A dermatoscopic image of a skin lesion; the subject is a female aged approximately 20:
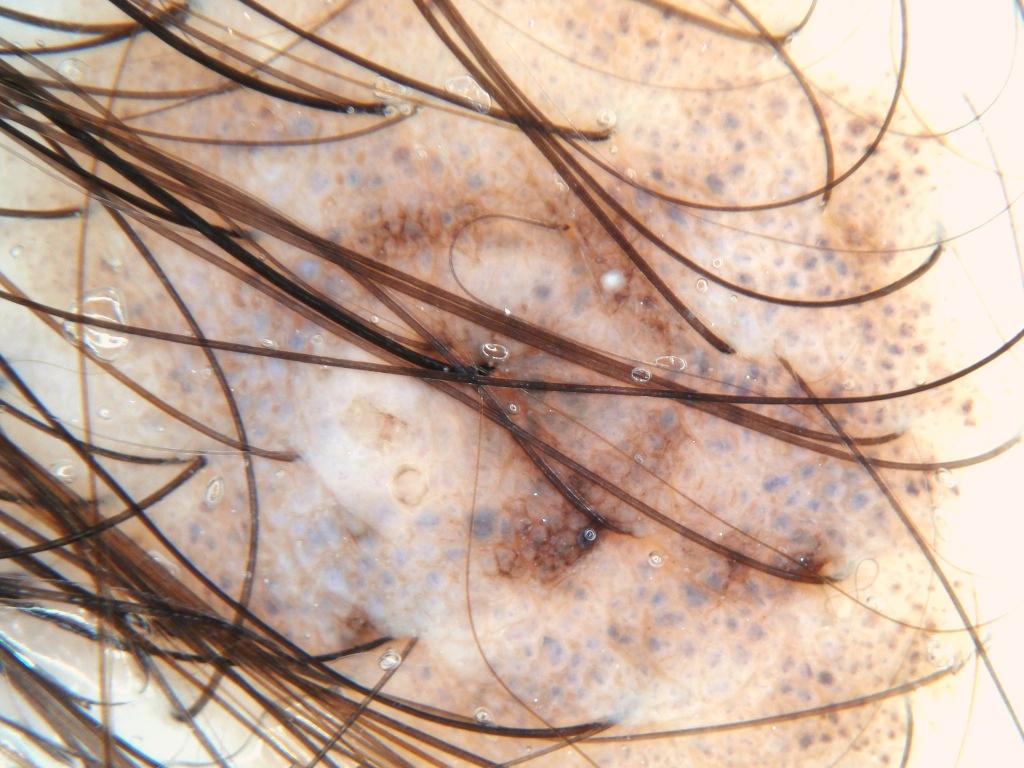Dermoscopic review identifies milia-like cysts and pigment network.
The lesion spans essentially the entire dermoscopic field.
The clinical diagnosis was a melanocytic nevus.